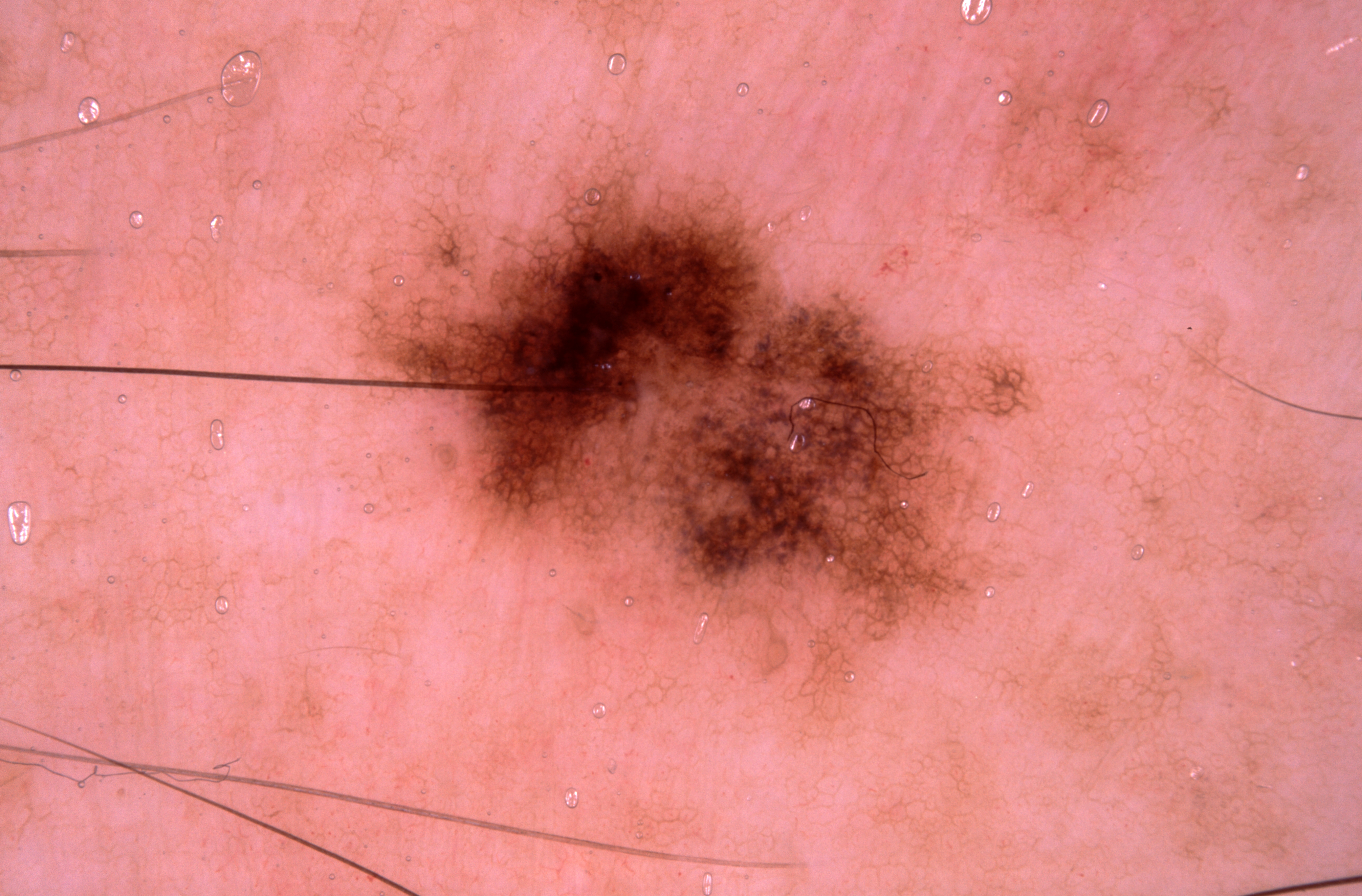The patient is a male aged approximately 80. A dermatoscopic image of a skin lesion. The lesion occupies roughly 24% of the field. The lesion is located at x1=340, y1=131, x2=1047, y2=761. The dermoscopic pattern shows pigment network. The clinical diagnosis was a melanocytic nevus.